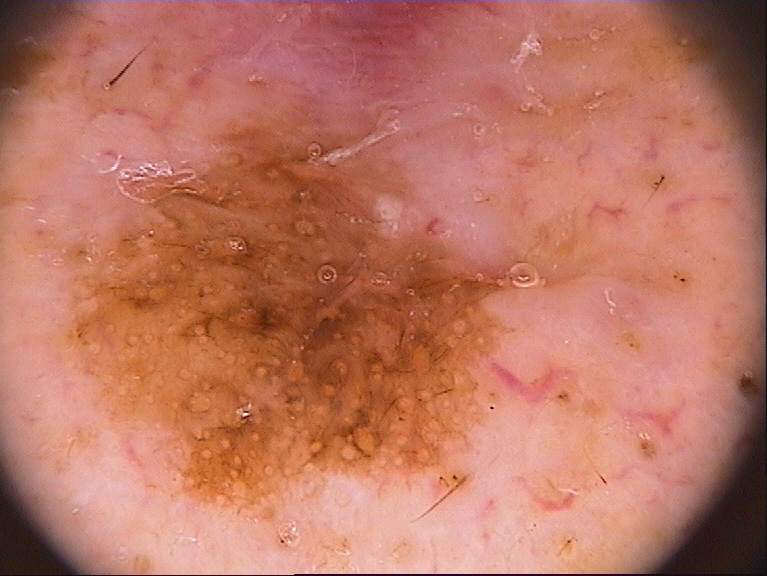Findings: A male subject. A dermoscopy image of a single skin lesion. The dermoscopic pattern shows no globules, milia-like cysts, pigment network, negative network, or streaks. The lesion occupies the region x1=33 y1=77 x2=544 y2=538. Assessment: The clinical diagnosis was a melanocytic nevus.